Dermoscopy of a skin lesion: 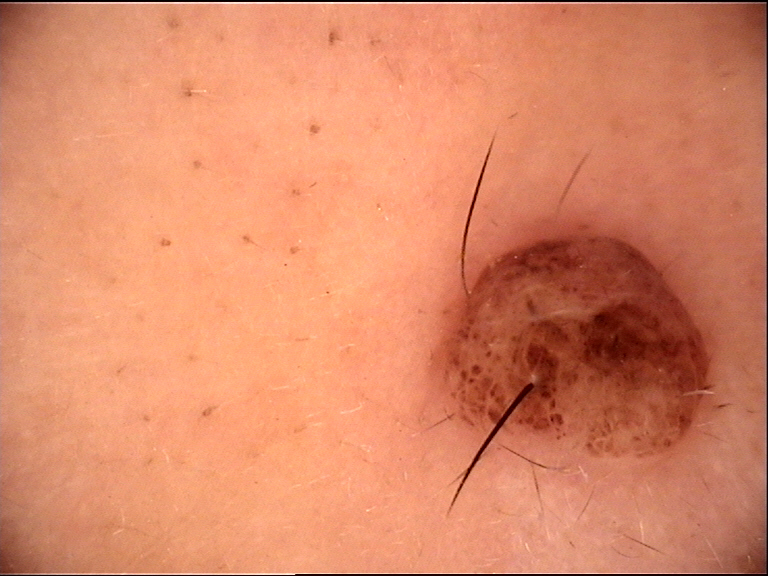<dermoscopy>
<lesion_type>
<main_class>banal</main_class>
<pattern>dermal</pattern>
</lesion_type>
<diagnosis>
<name>dermal nevus</name>
<code>db</code>
<malignancy>benign</malignancy>
<super_class>melanocytic</super_class>
<confirmation>expert consensus</confirmation>
</diagnosis>
</dermoscopy>